Imaged for a research study, with no referral diagnosis recorded; a male patient aged 65; the patient says their skin tans without first burning; a skin lesion imaged with a dermatoscope; the patient describes having a moderate number of moles:
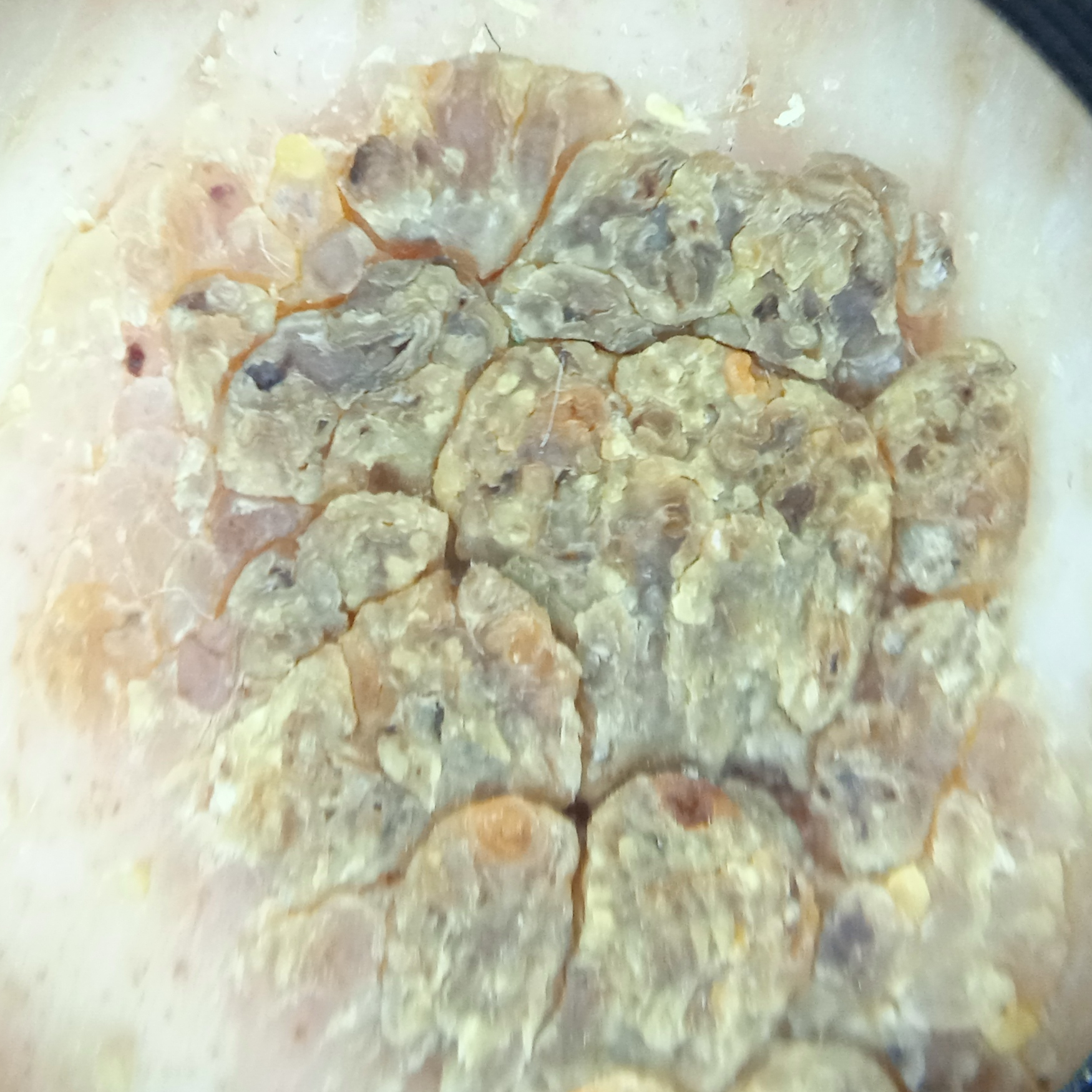{"lesion_location": "the back", "lesion_size": {"diameter_mm": 18.8}, "diagnosis": {"name": "seborrheic keratosis", "malignancy": "benign", "unanimous": false, "certainty": "good", "second_options": ["a squamous cell carcinoma"]}}